An image taken at a distance · present for one to three months · the patient indicates bothersome appearance and itching · female subject, age 18–29 · the patient considered this a rash: 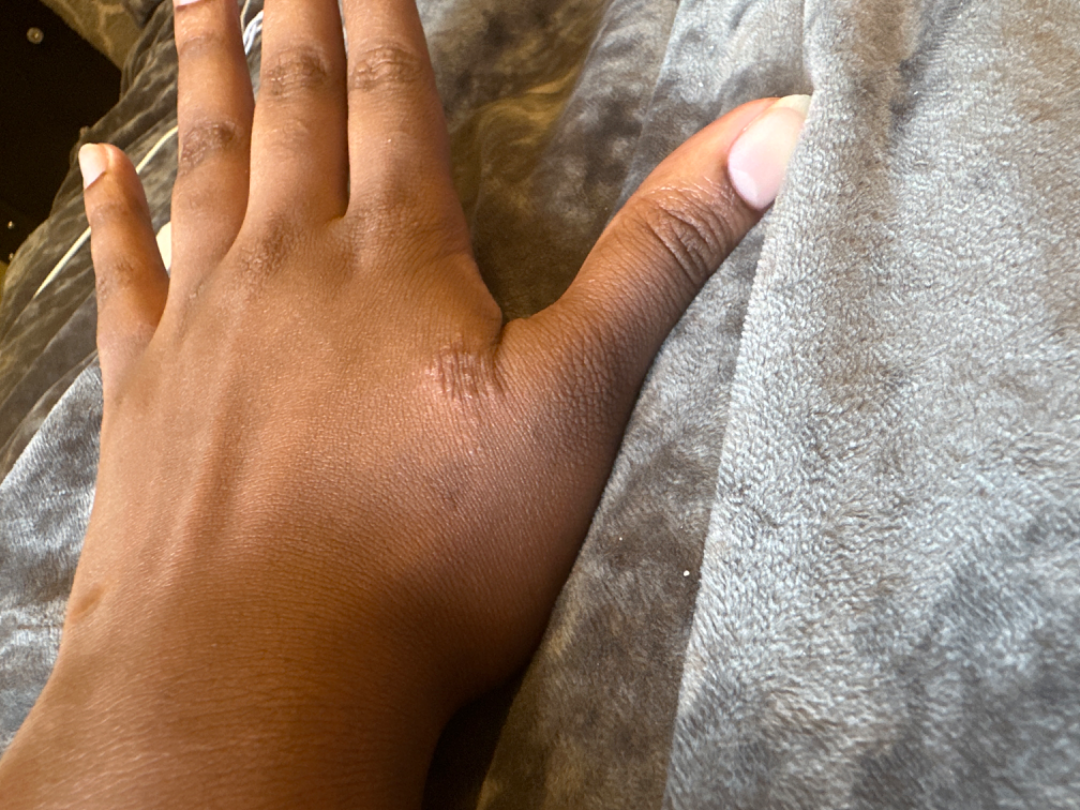{"differential": ["Acute and chronic dermatitis", "Allergic Contact Dermatitis", "Irritant Contact Dermatitis"]}